A dermatoscopic image of a skin lesion. A male patient aged approximately 15 — 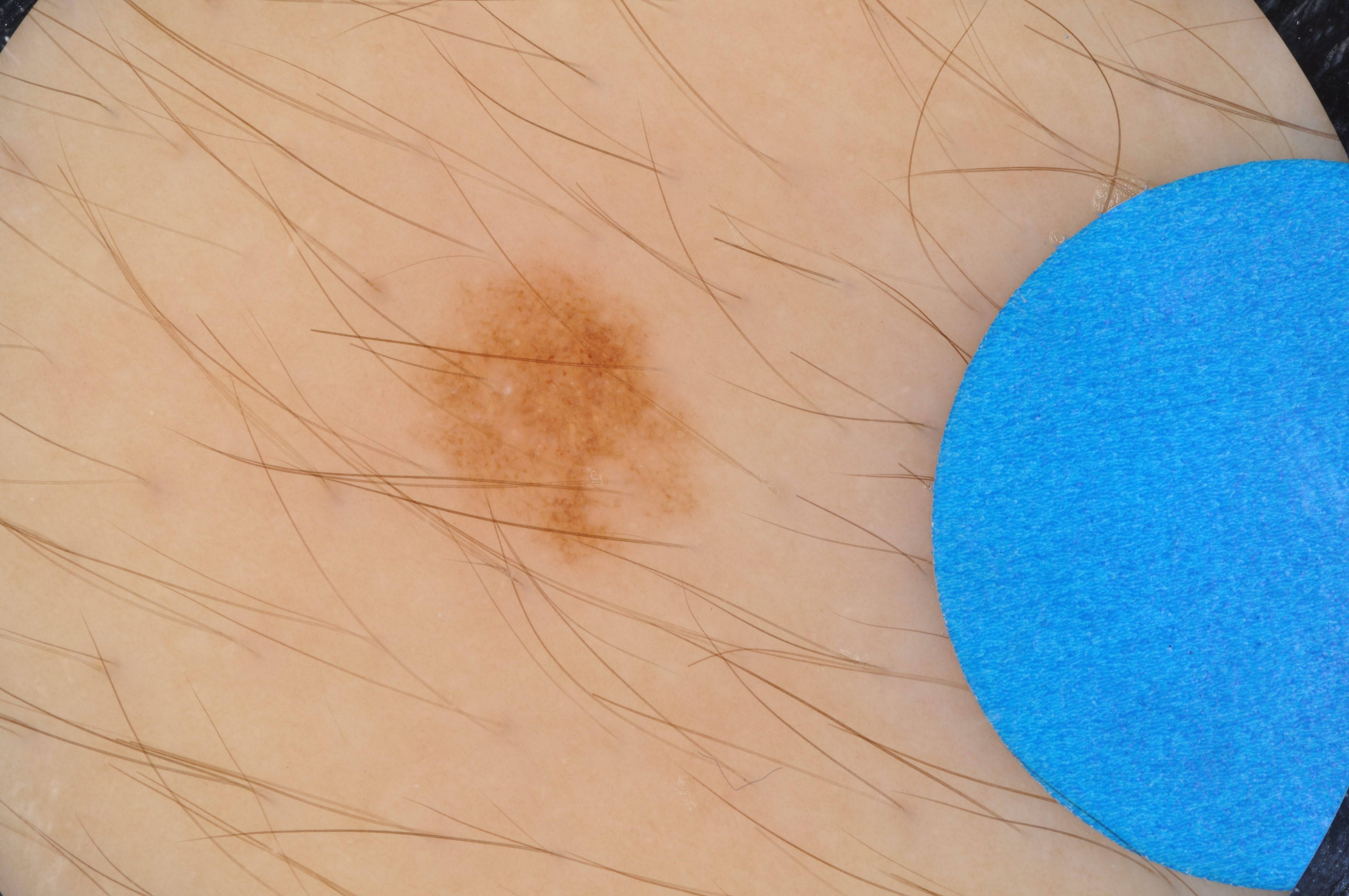Q: Lesion extent?
A: small
Q: Where is the lesion in the image?
A: 373/239/723/575
Q: Which dermoscopic features were noted?
A: pigment network, globules, and milia-like cysts; absent: negative network and streaks
Q: What did the assessment conclude?
A: a melanocytic nevus, a benign skin lesion